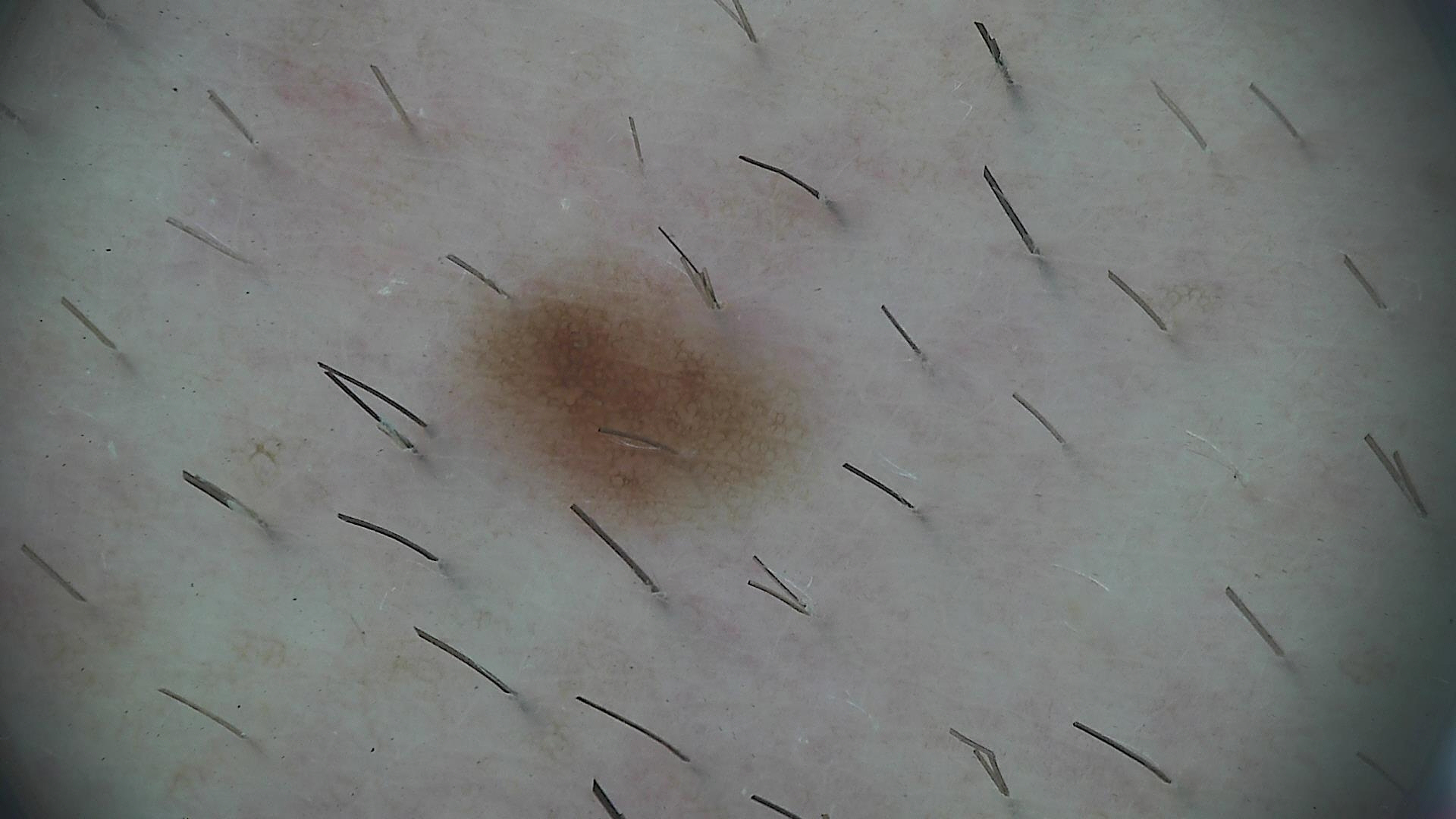diagnostic label — dysplastic junctional nevus (expert consensus).